A clinical photograph showing a skin lesion · a female patient age 89:
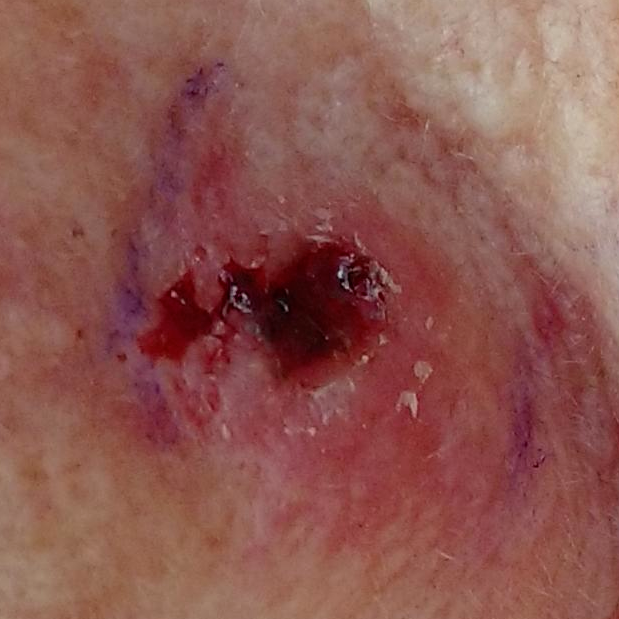Q: Where on the body is the lesion?
A: the nose
Q: Any reported symptoms?
A: elevation, itching, pain, bleeding
Q: What is this lesion?
A: actinic keratosis (biopsy-proven)